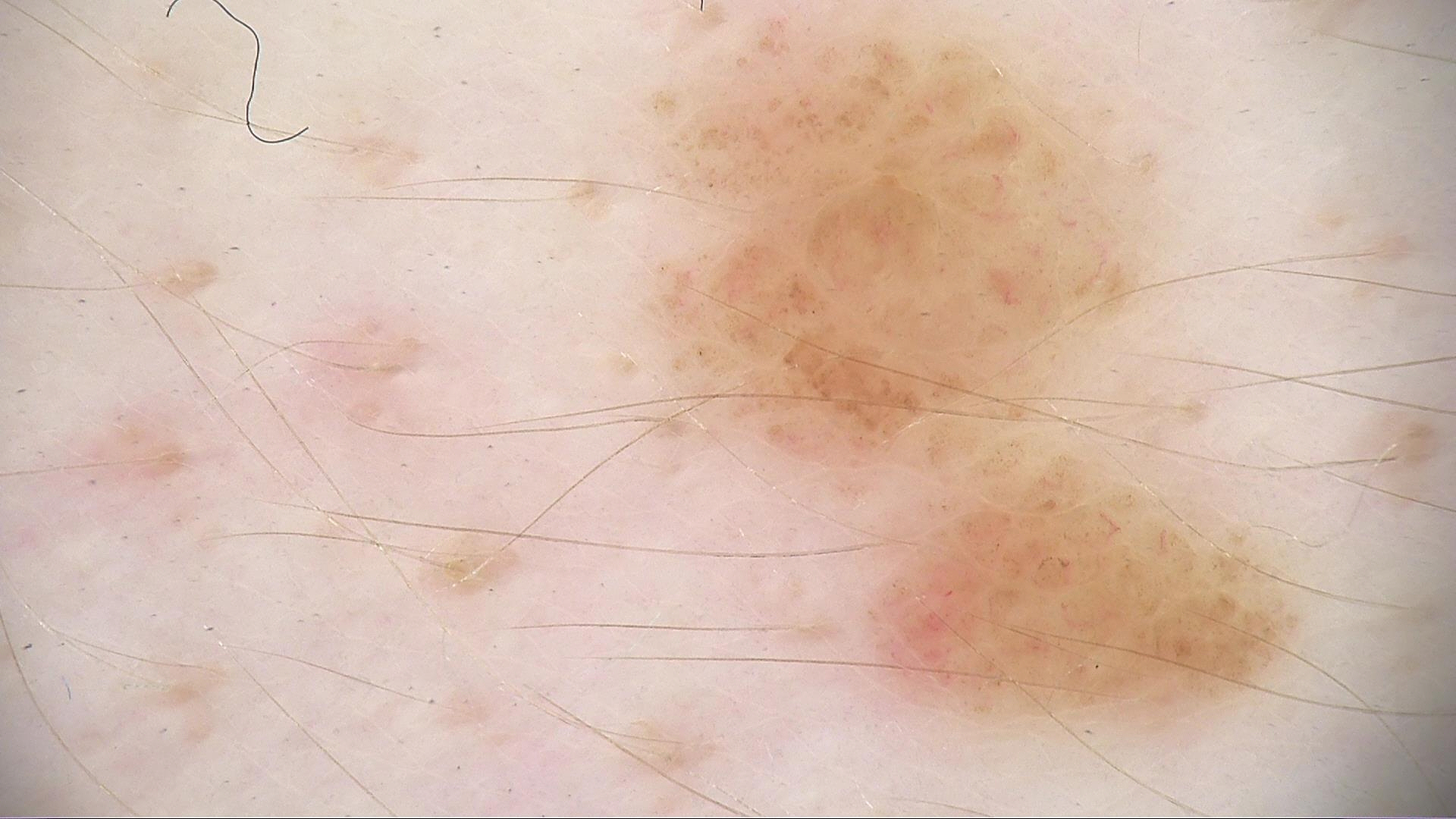class=junctional nevus (expert consensus)